A dermatoscopic image of a skin lesion; the patient is a male approximately 85 years of age or older.
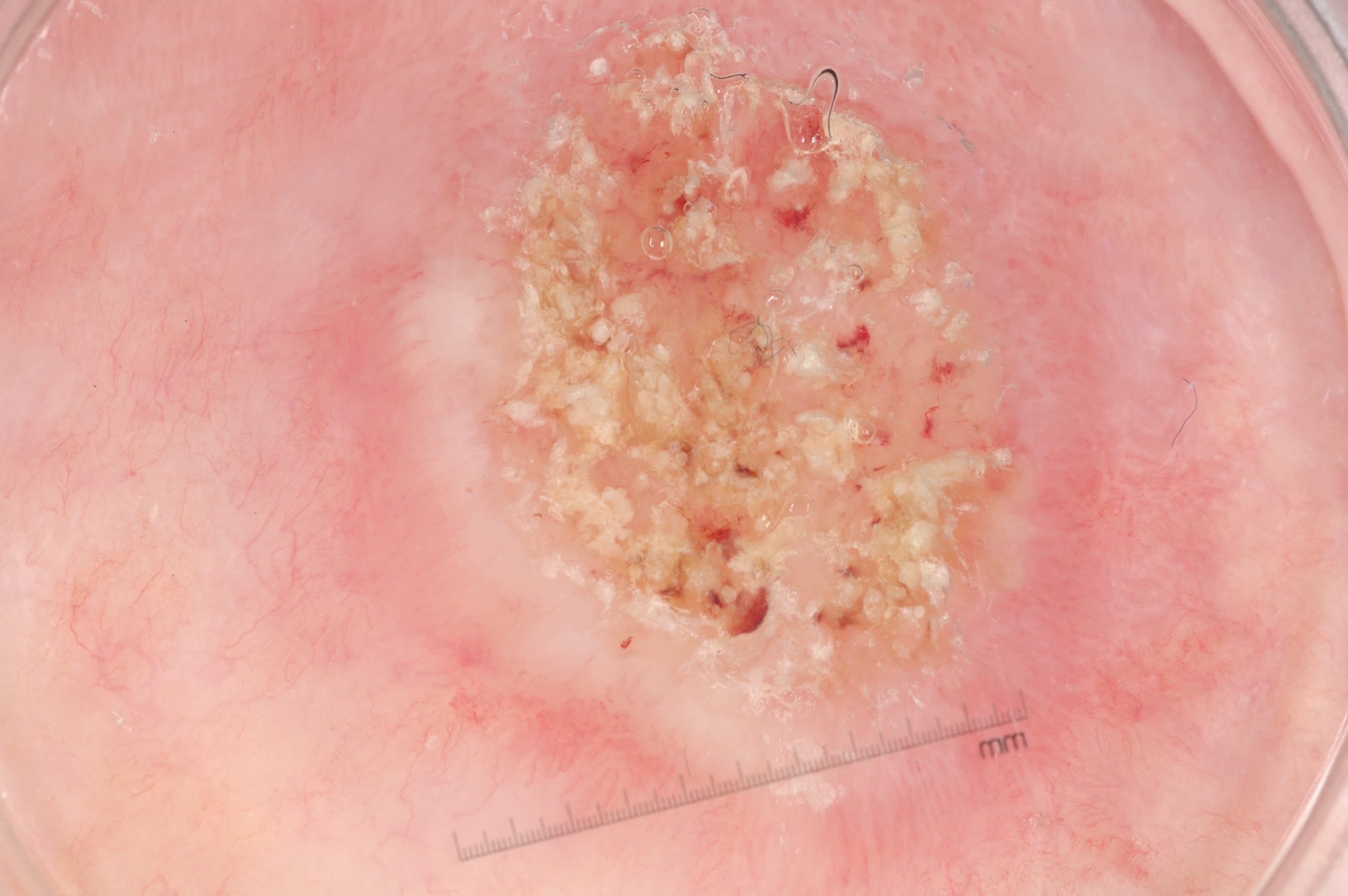dermoscopic features assessed but absent=milia-like cysts, streaks, negative network, and pigment network
lesion location=<bbox>318, 5, 1131, 867</bbox>
assessment=a seborrheic keratosis, a benign lesion